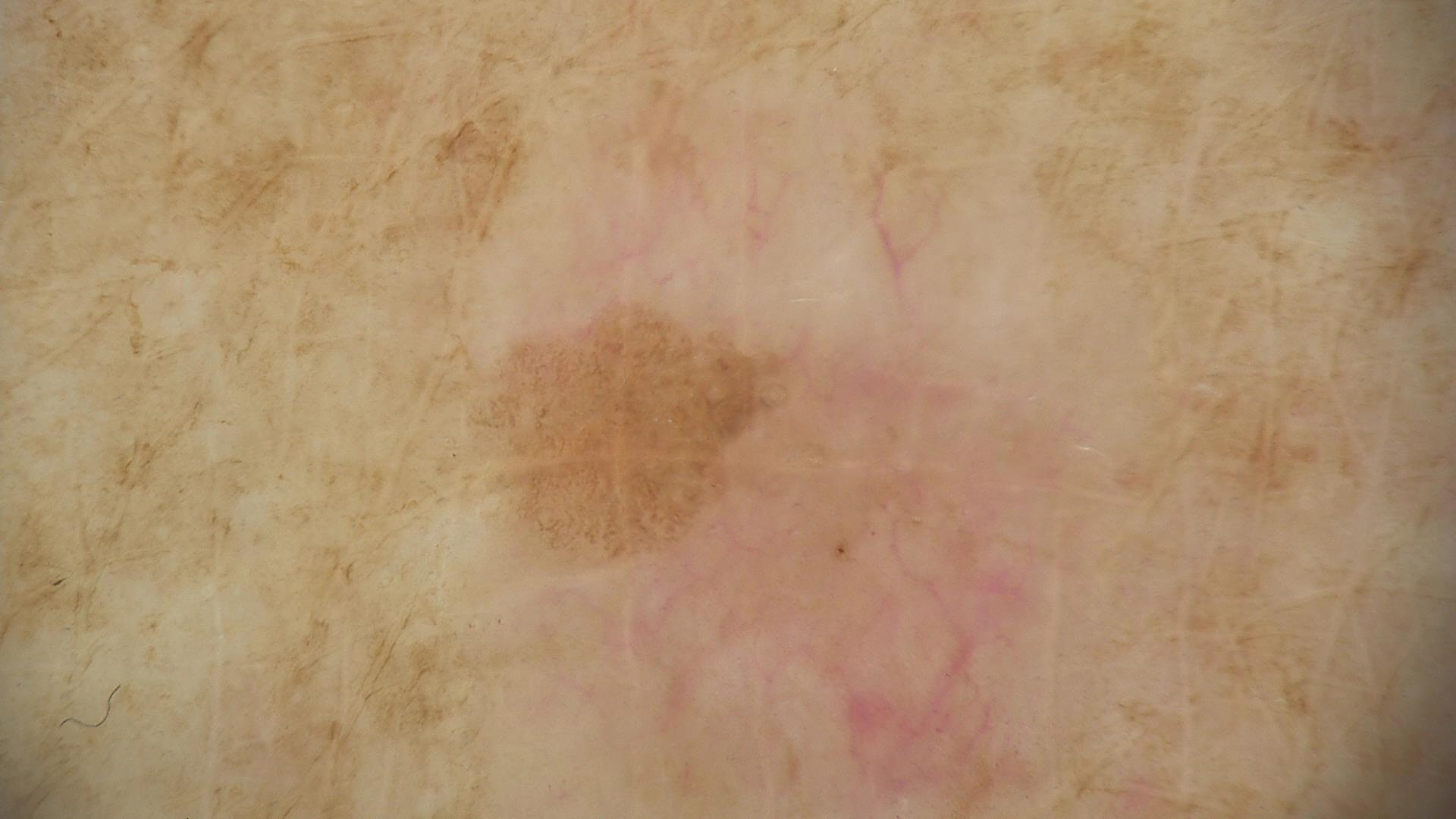Summary:
A dermatoscopic image of a skin lesion.
Impression:
The diagnosis was a keratinocytic, benign lesion — a seborrheic keratosis.